This image was taken at an angle, skin tone: Fitzpatrick III; human graders estimated Monk skin tone scale 1 or 2 (two reviewer pools), the condition has been present for one to four weeks, located on the leg:
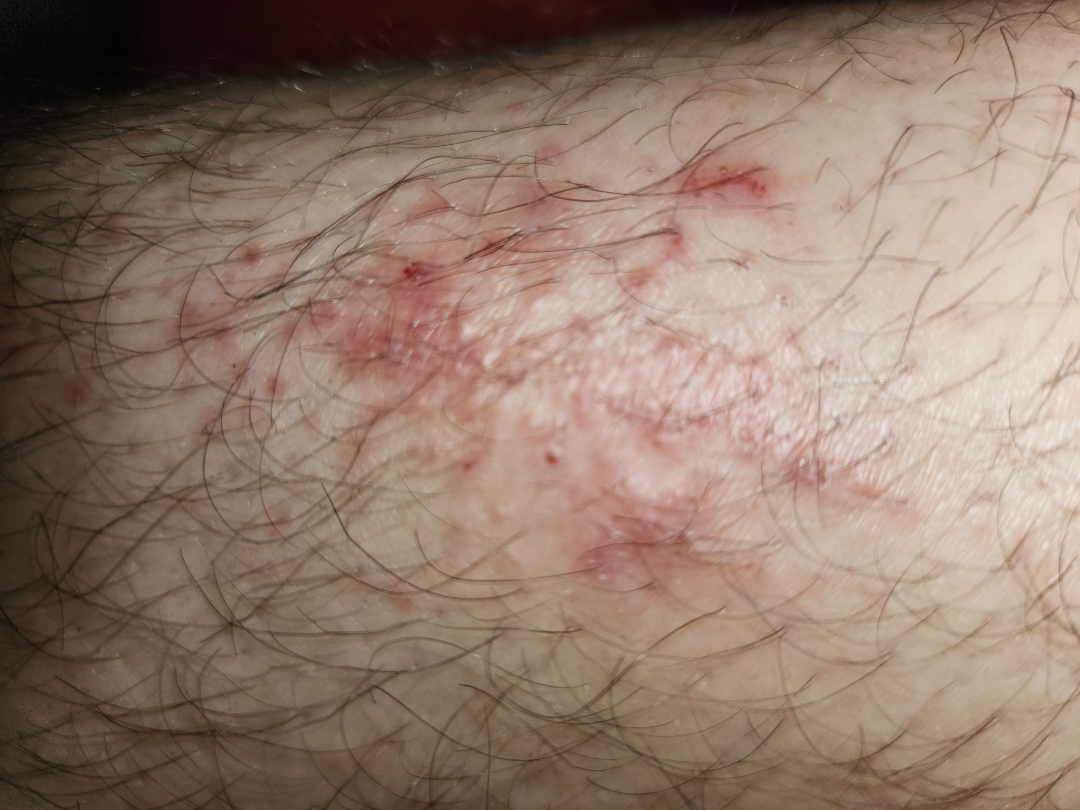Impression:
The reviewer was unable to grade this case for skin condition.